Close-up view, the lesion involves the arm:
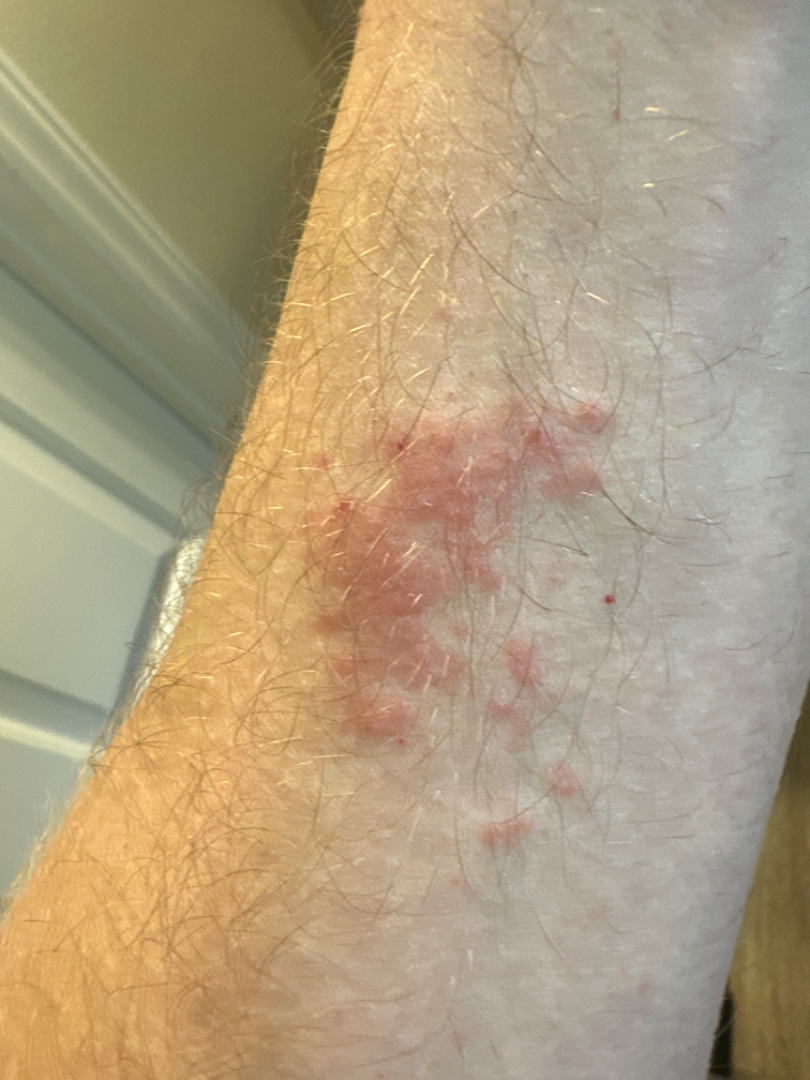Q: Could the case be diagnosed?
A: indeterminate
Q: What is the lesion texture?
A: flat
Q: Reported symptoms?
A: bothersome appearance and itching
Q: Duration?
A: less than one week